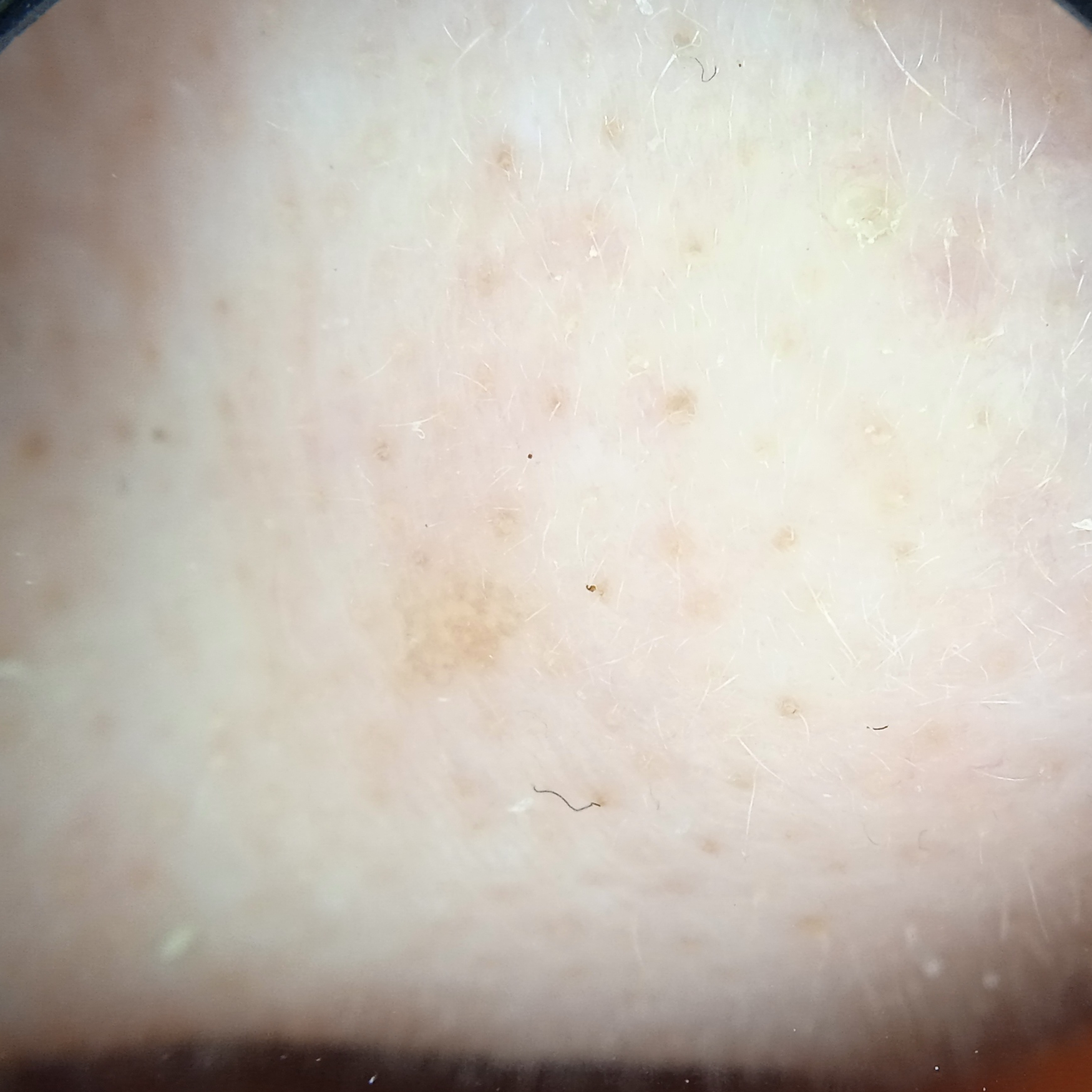Conclusion: The consensus diagnosis for this lesion was an actinic keratosis.